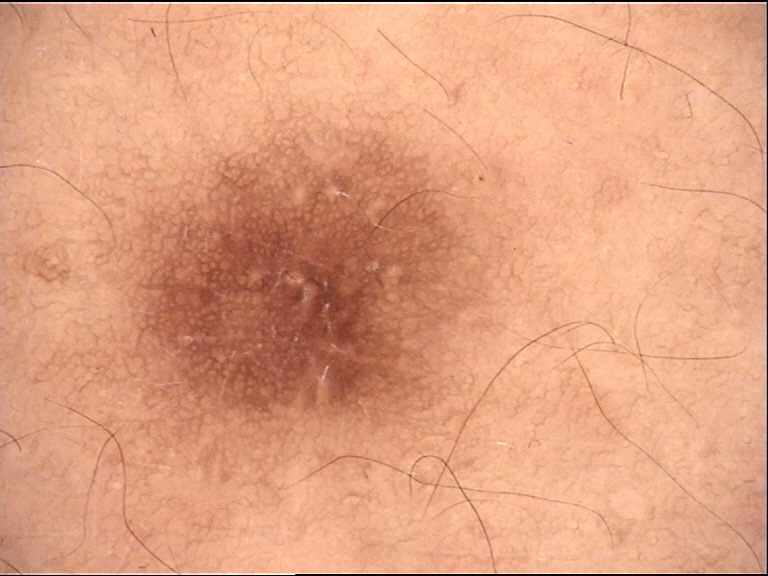| feature | finding |
|---|---|
| class | dermatofibroma (expert consensus) |